The patient is 18–29, male; a close-up photograph; located on the arm and palm.
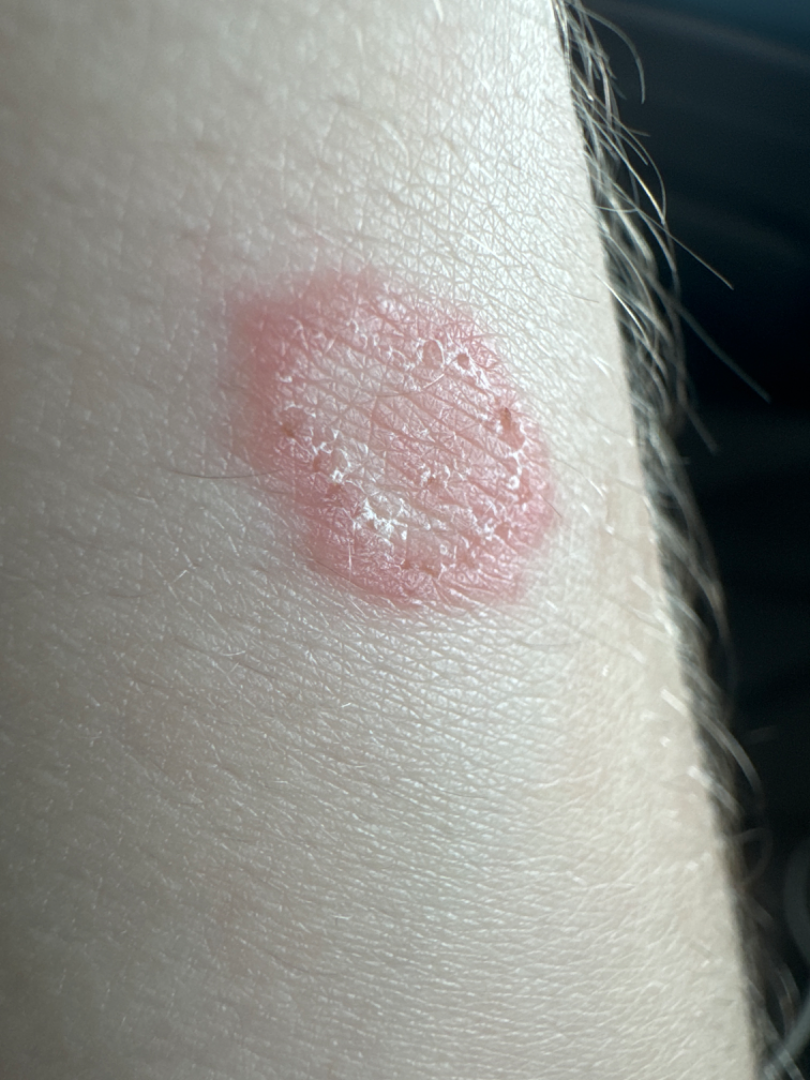Impression: On remote review of the image, the impression was split between Tinea and Eczema; less probable is Psoriasis.